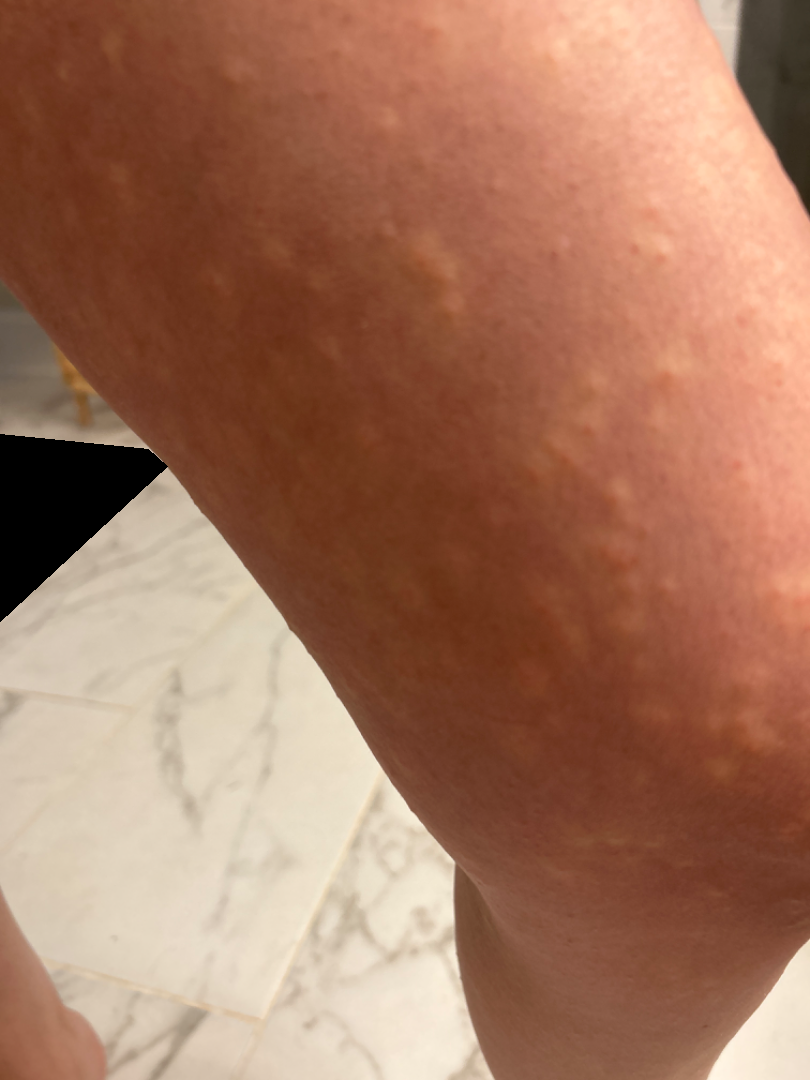{
  "assessment": "could not be assessed",
  "shot_type": "close-up",
  "systemic_symptoms": "fatigue",
  "body_site": "leg"
}